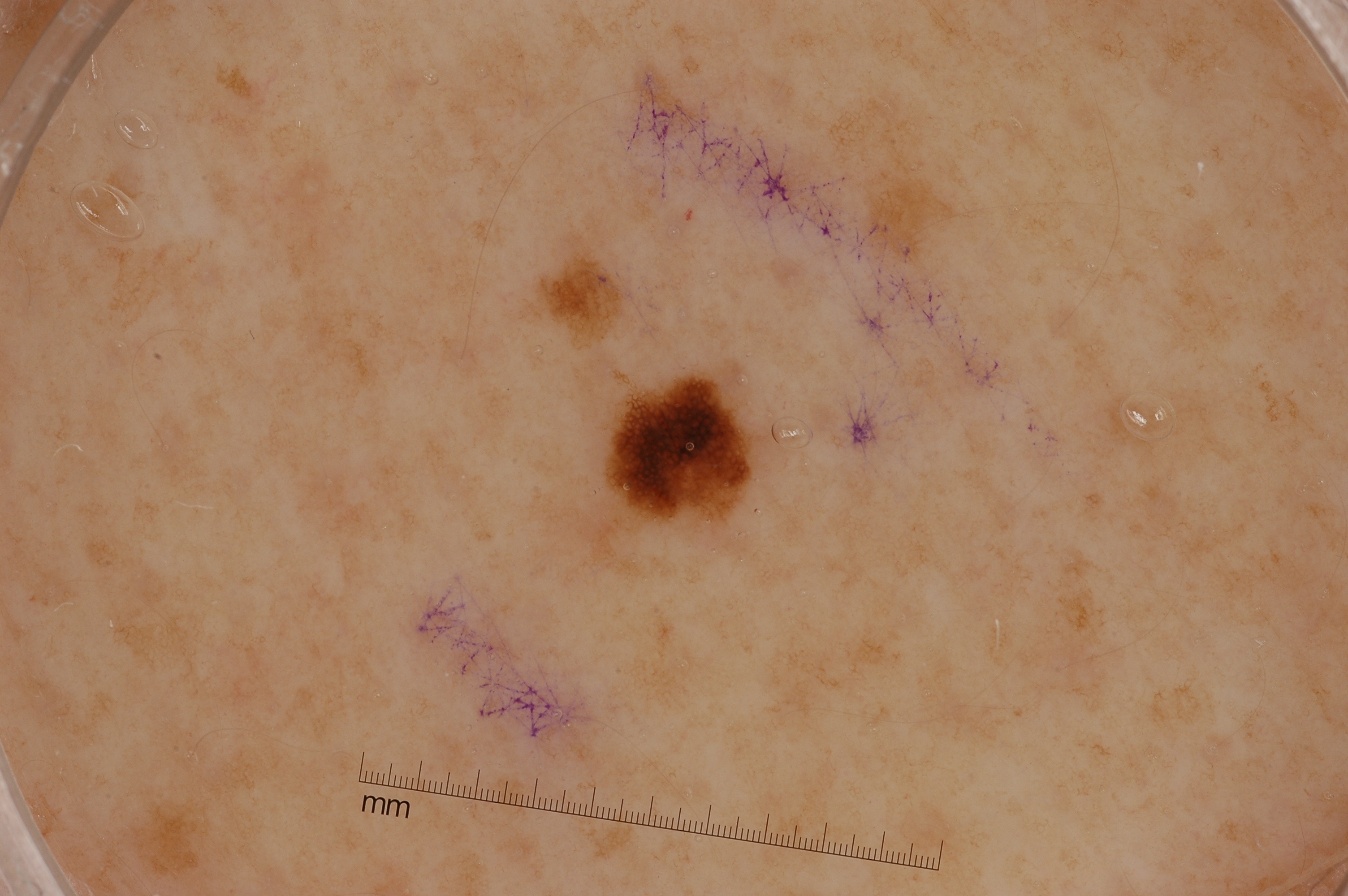Case summary:
- image type — dermoscopy of a skin lesion
- extent — small
- features — pigment network; absent: milia-like cysts, negative network, and streaks
- lesion location — x1=611 y1=385 x2=758 y2=518
- diagnostic label — a melanocytic nevus